A skin lesion imaged with a dermatoscope. A male patient, aged approximately 40: 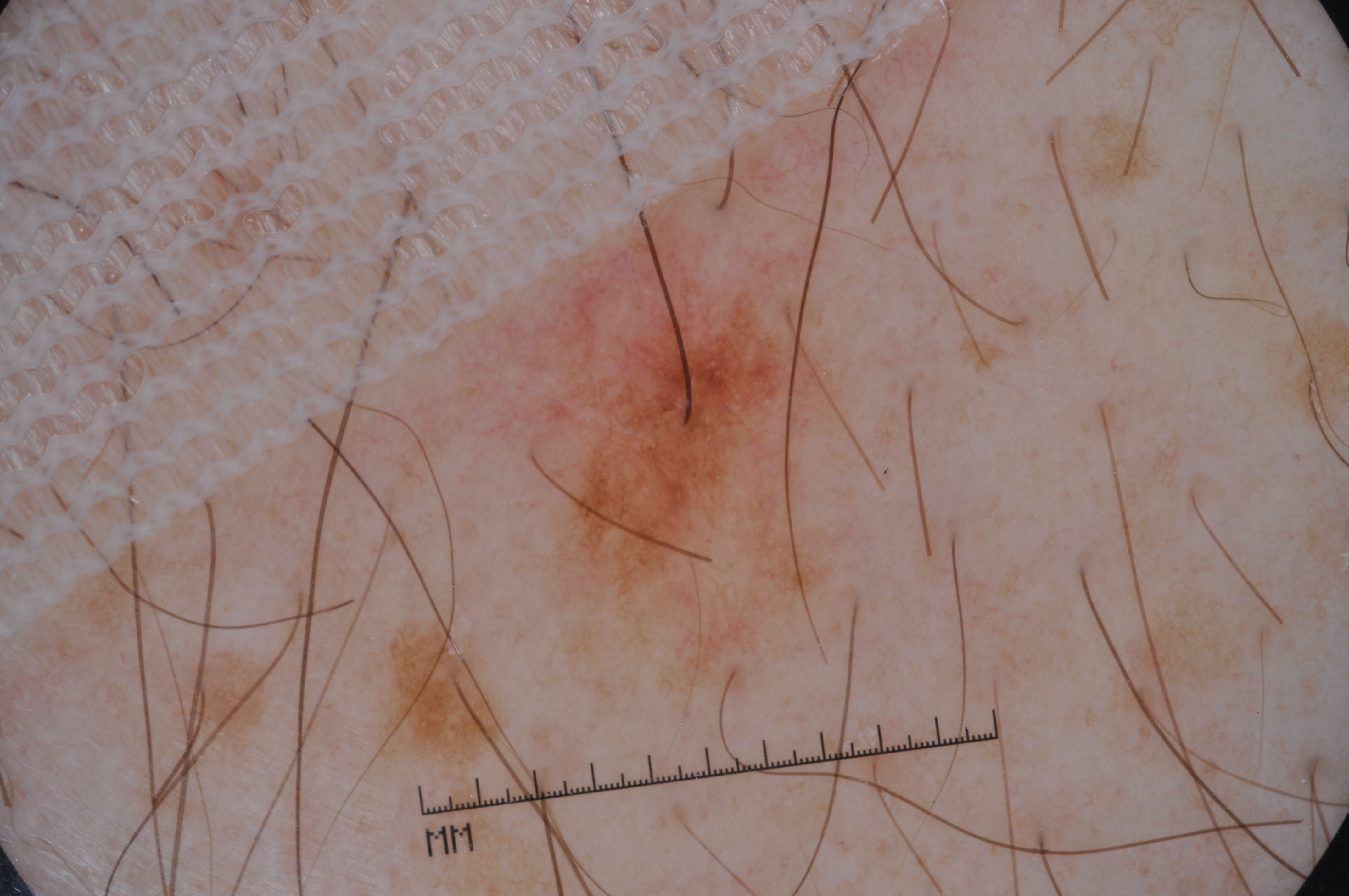Dermoscopy demonstrates pigment network and milia-like cysts, with no streaks or negative network. The lesion occupies the region 474, 203, 843, 602. Diagnosed as a melanocytic nevus.